A dermoscopic photograph of a skin lesion.
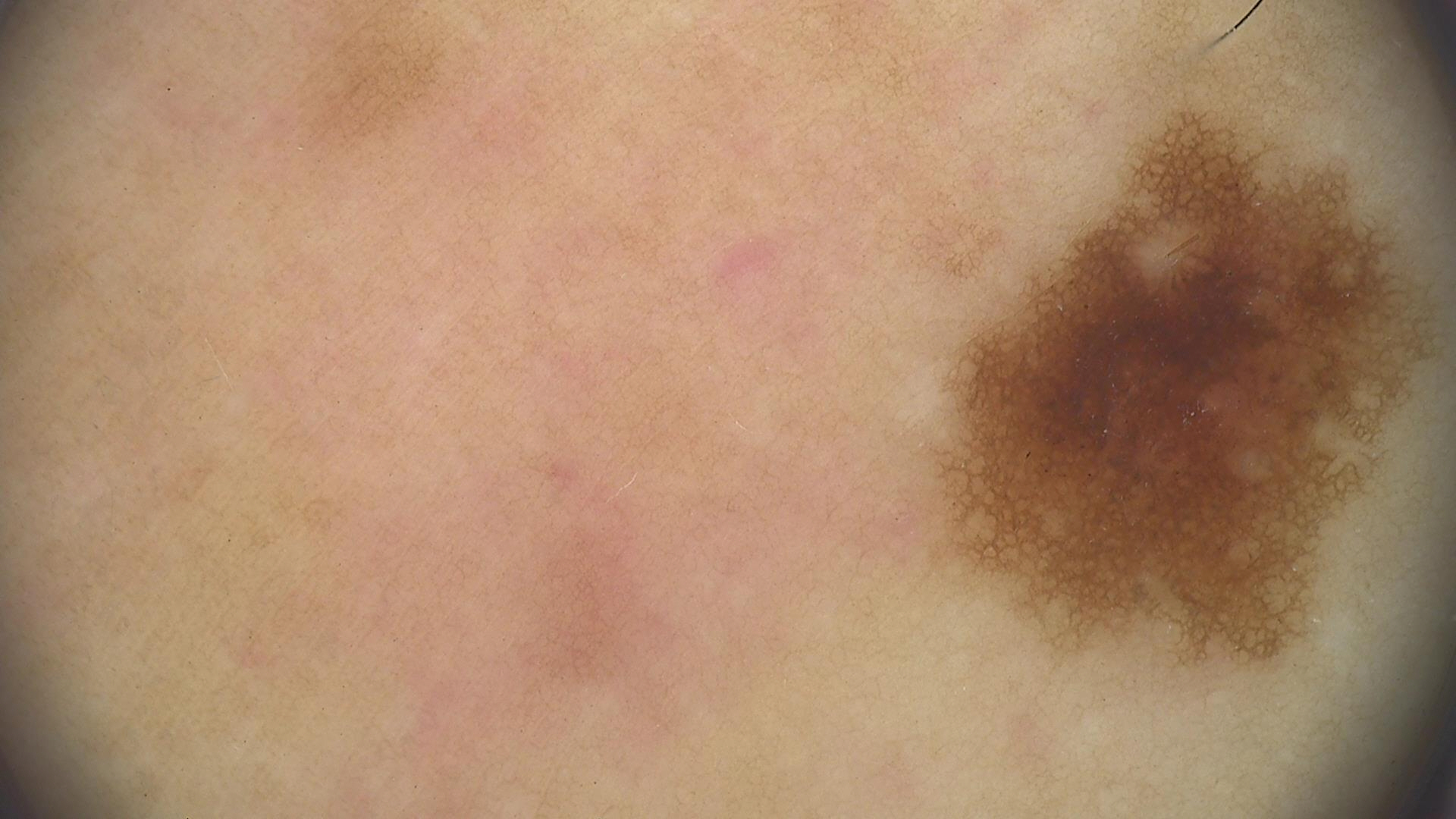Consistent with a benign lesion — a dysplastic junctional nevus.